This image was taken at a distance · the patient notes the lesion is rough or flaky · female subject, age 40–49 · reported duration is more than one year · the patient reported no systemic symptoms · the leg, arm and back of the hand are involved · self-reported Fitzpatrick I.
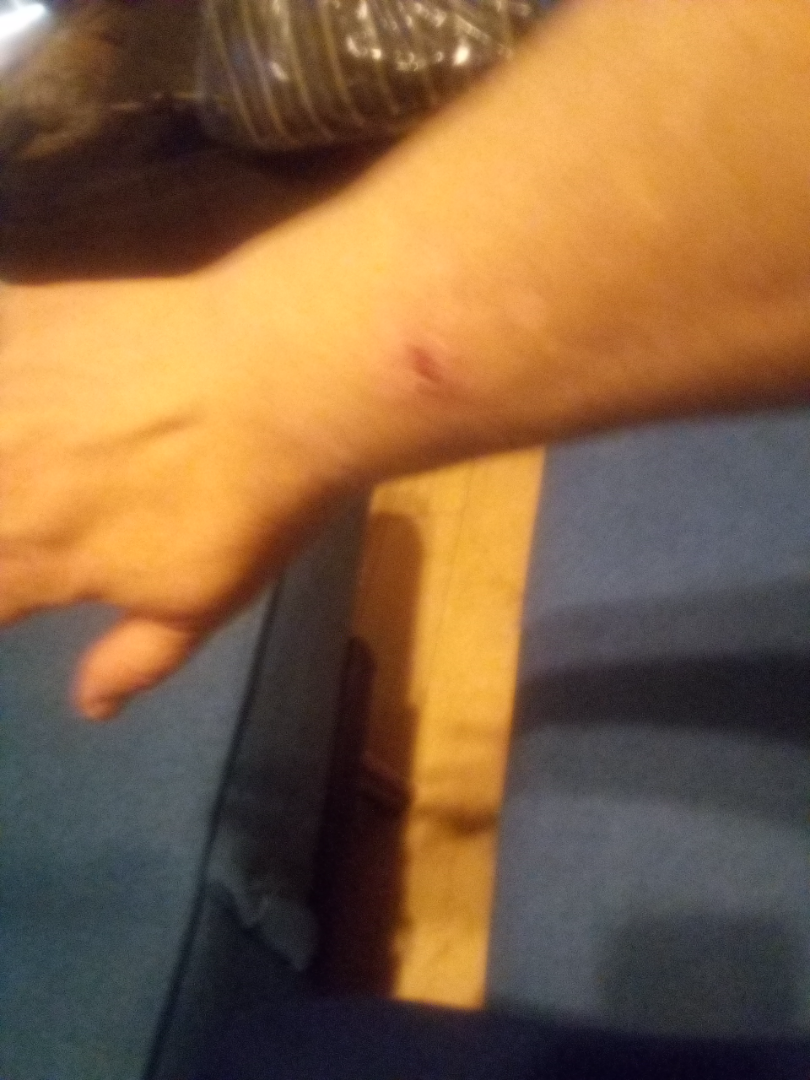Review: The image was not sufficient for the reviewer to characterize the skin condition.